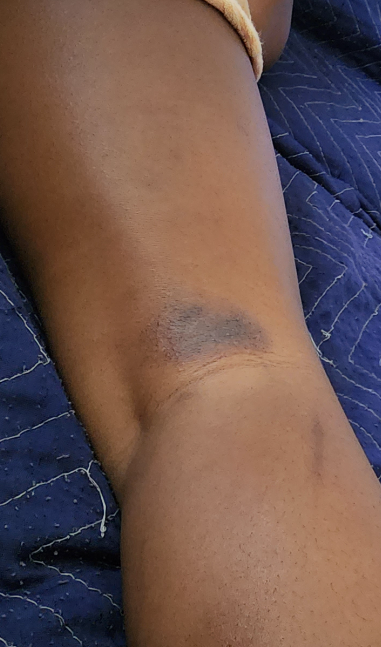| feature | finding |
|---|---|
| differential diagnosis | Lichen Simplex Chronicus (primary); Lichen planus/lichenoid eruption (possible); ecchymoses (less likely) |